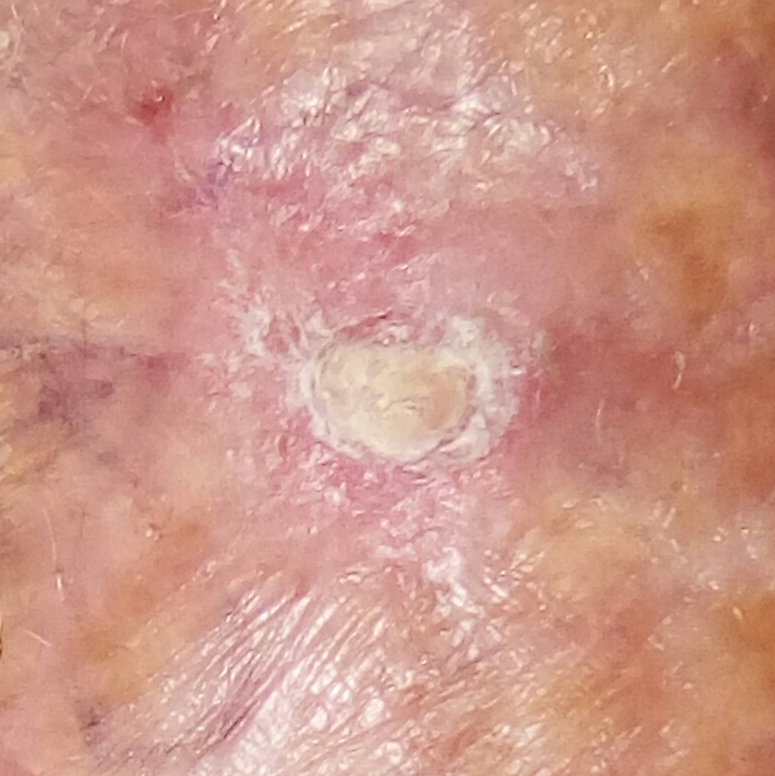Q: What is the patient's skin type?
A: II
Q: What kind of image is this?
A: clinical photograph
Q: What is the anatomic site?
A: a forearm
Q: What is this lesion?
A: actinic keratosis (biopsy-proven)